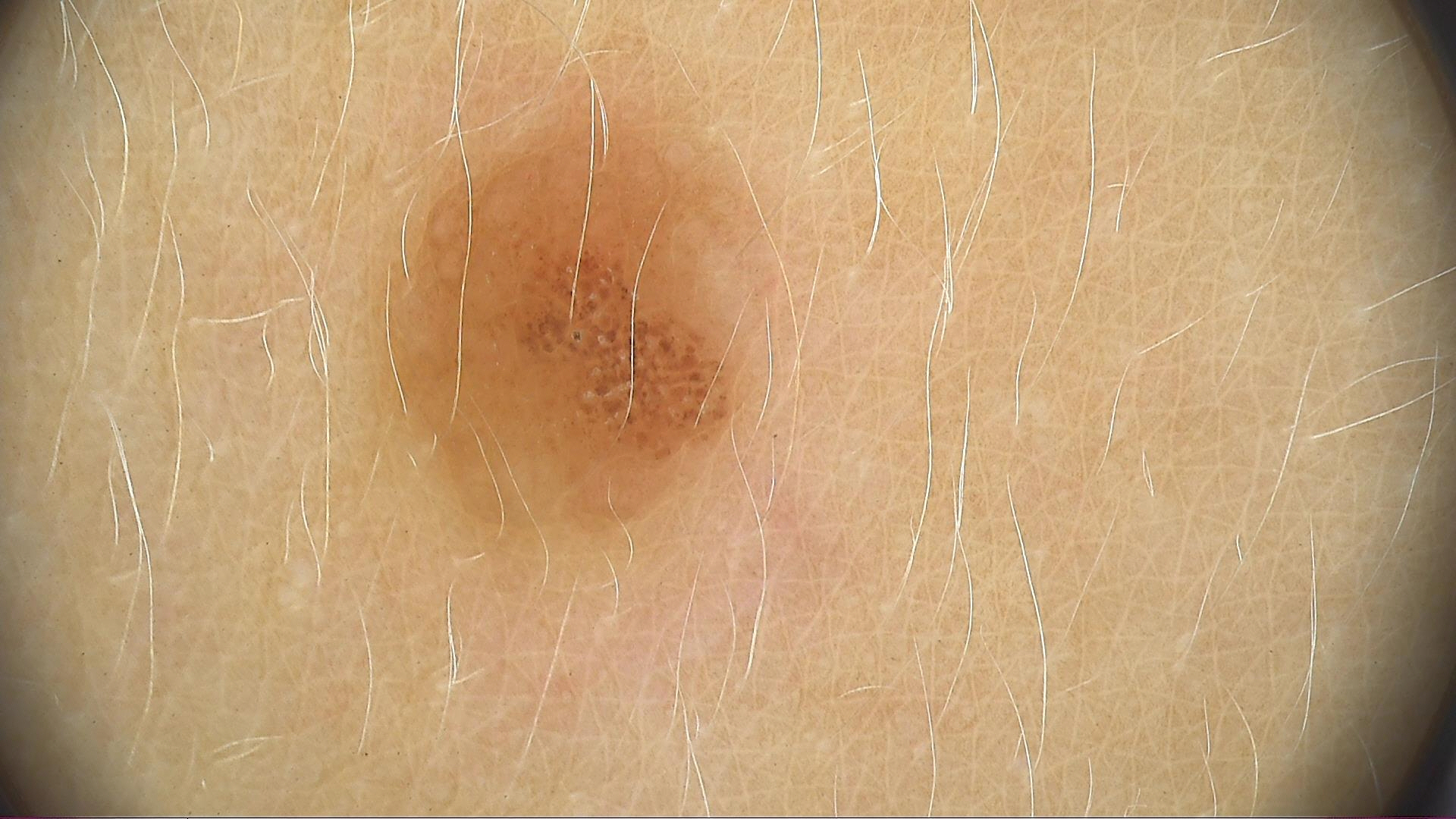A skin lesion imaged with a dermatoscope. This is a banal lesion. The diagnosis was a dermal nevus.